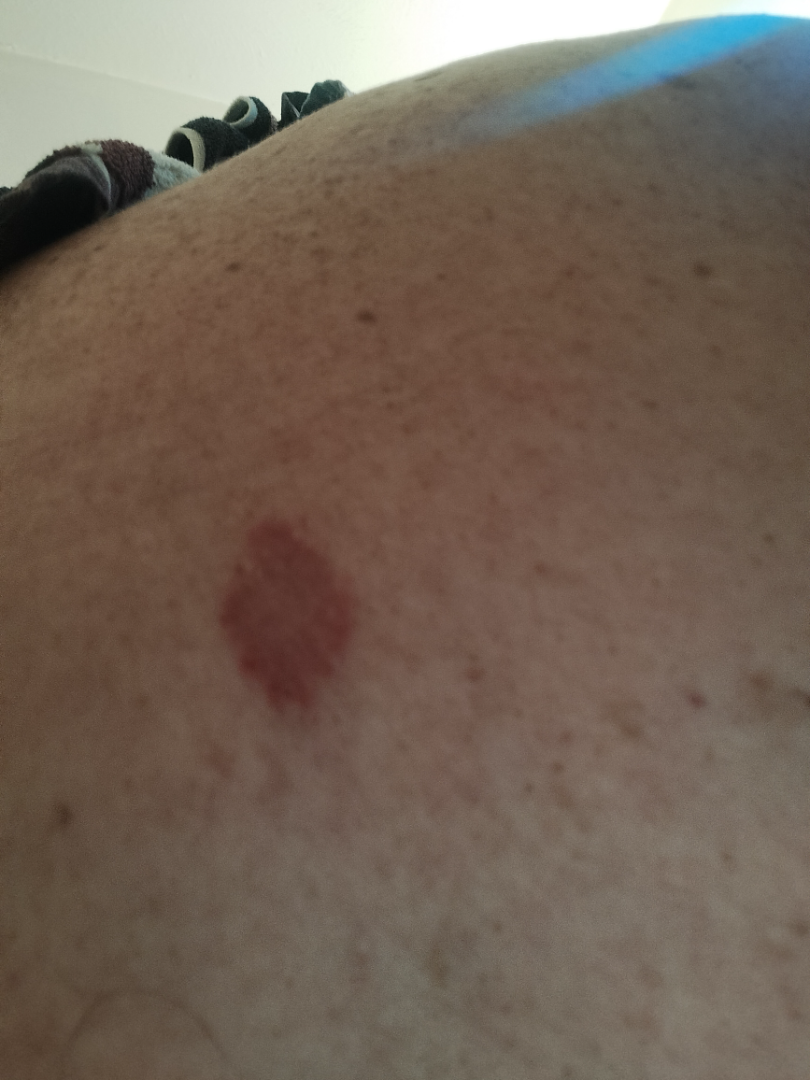Q: Where on the body?
A: back of the torso
Q: Age and sex?
A: female, age 50–59
Q: Constitutional symptoms?
A: none reported
Q: Texture?
A: rough or flaky
Q: What symptoms does the patient report?
A: bothersome appearance
Q: Image view?
A: at an angle
Q: What is the differential diagnosis?
A: the leading consideration is Basal Cell Carcinoma; also consider SCC/SCCIS; lower on the differential is Eczema